Dermoscopy of a skin lesion: 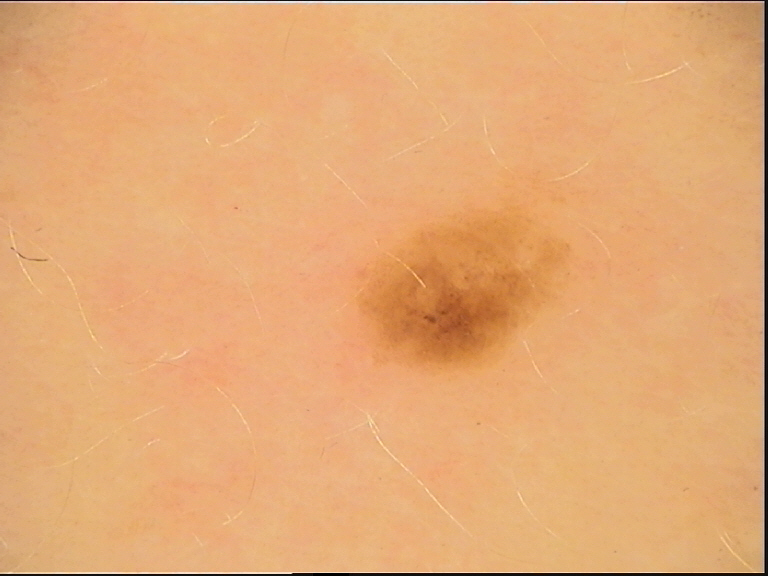The diagnosis was a benign lesion — a dysplastic junctional nevus.